Female subject, age 60–69 · an image taken at an angle · the top or side of the foot and leg are involved:
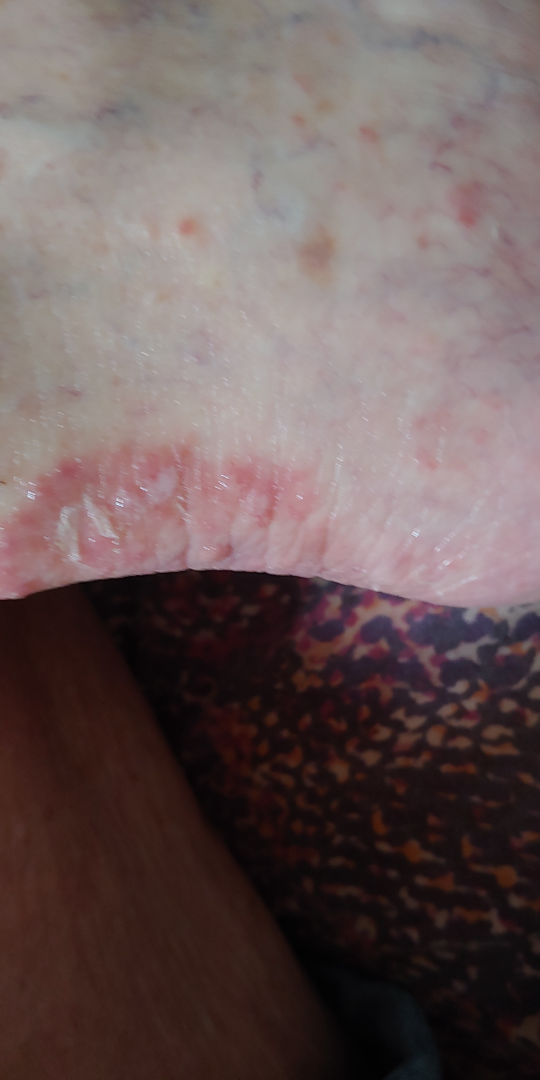The case was difficult to assess from the available photograph.